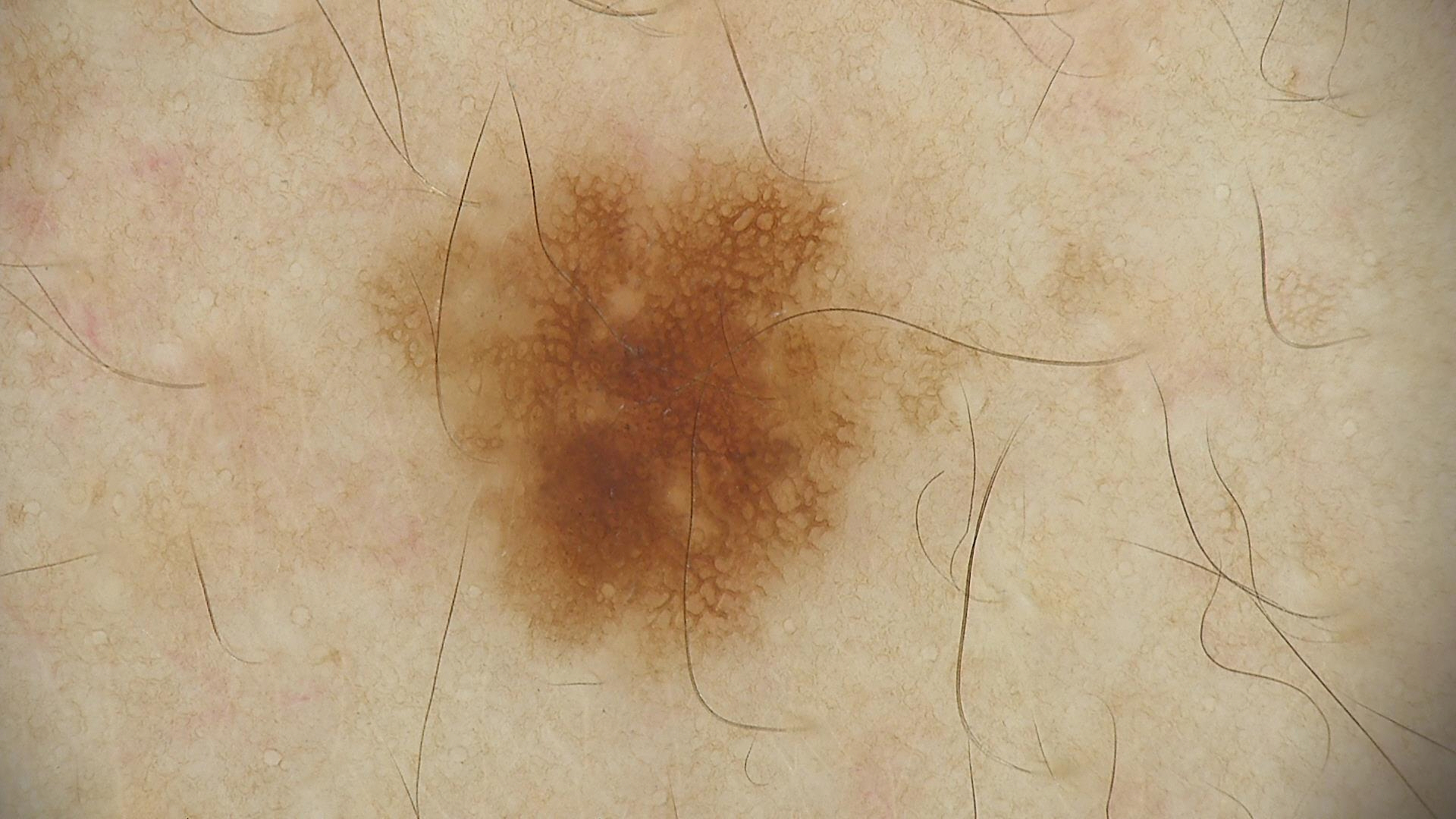Conclusion:
Classified as a benign lesion — a dysplastic junctional nevus.